Dermoscopy of a skin lesion.
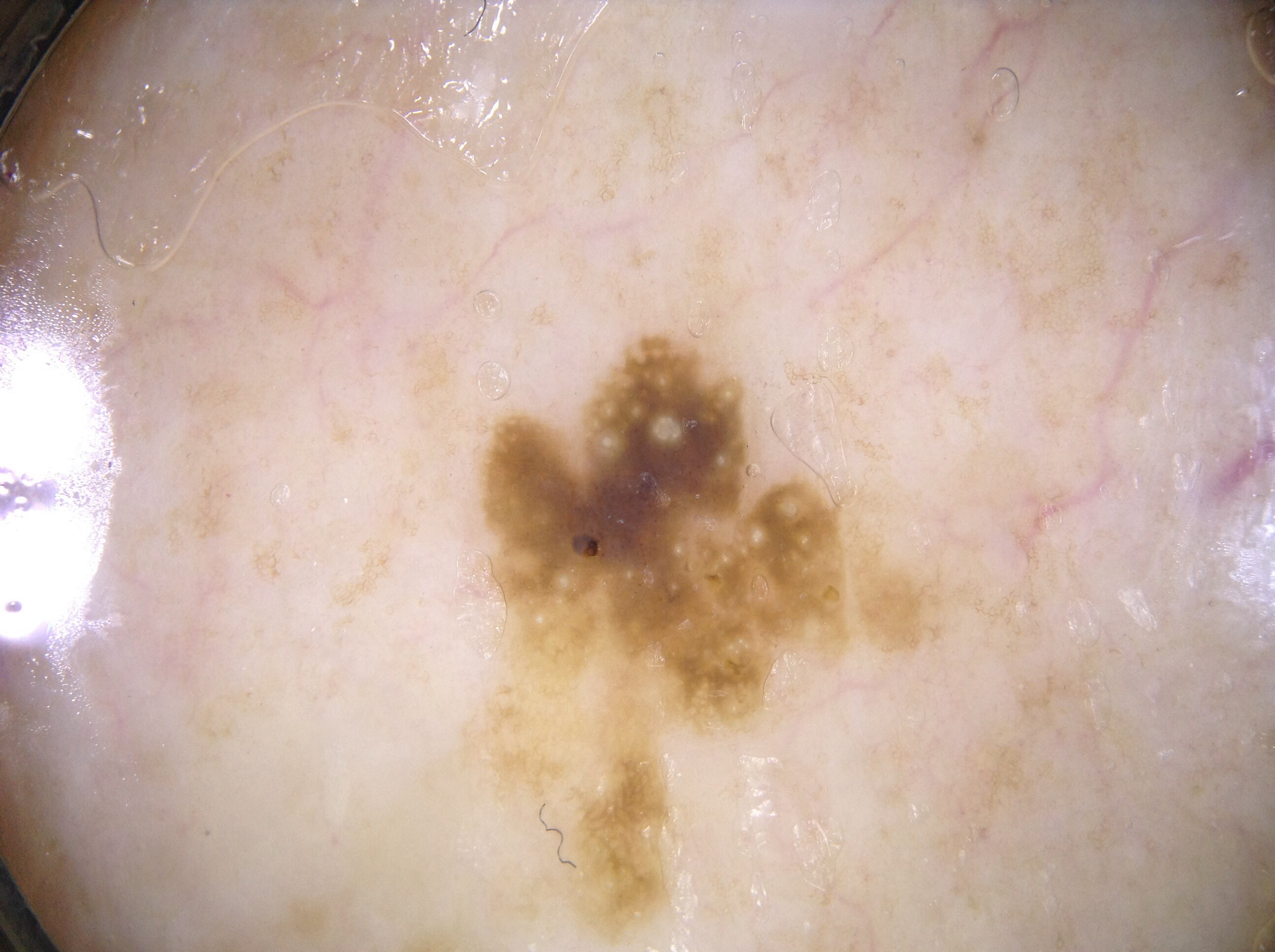| key | value |
|---|---|
| lesion size | moderate |
| location | 478, 327, 1025, 943 |
| dermoscopic findings | pigment network and milia-like cysts |
| impression | a seborrheic keratosis, a benign skin lesion |